Dermoscopy of a skin lesion.
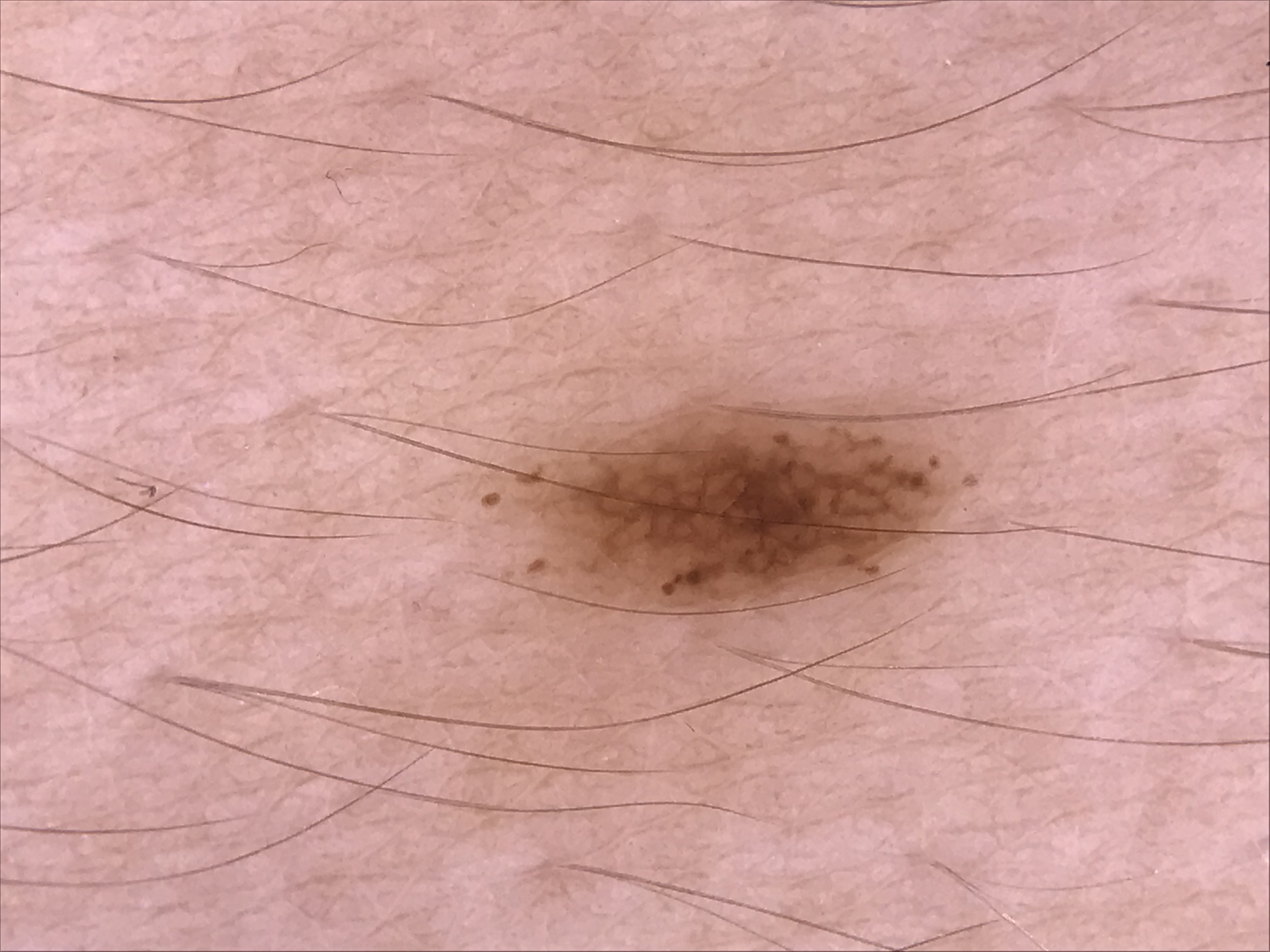The diagnosis was a benign lesion — a dysplastic junctional nevus.